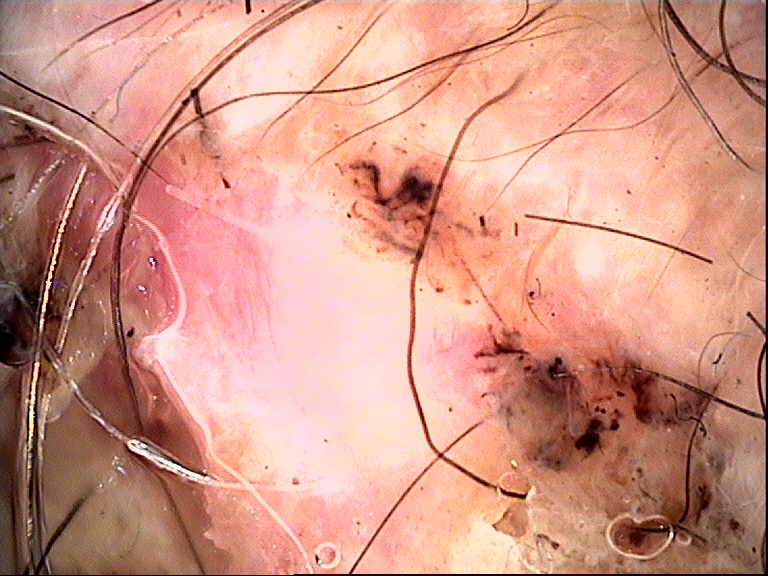Diagnosis: Confirmed on histopathology as a squamous cell carcinoma.